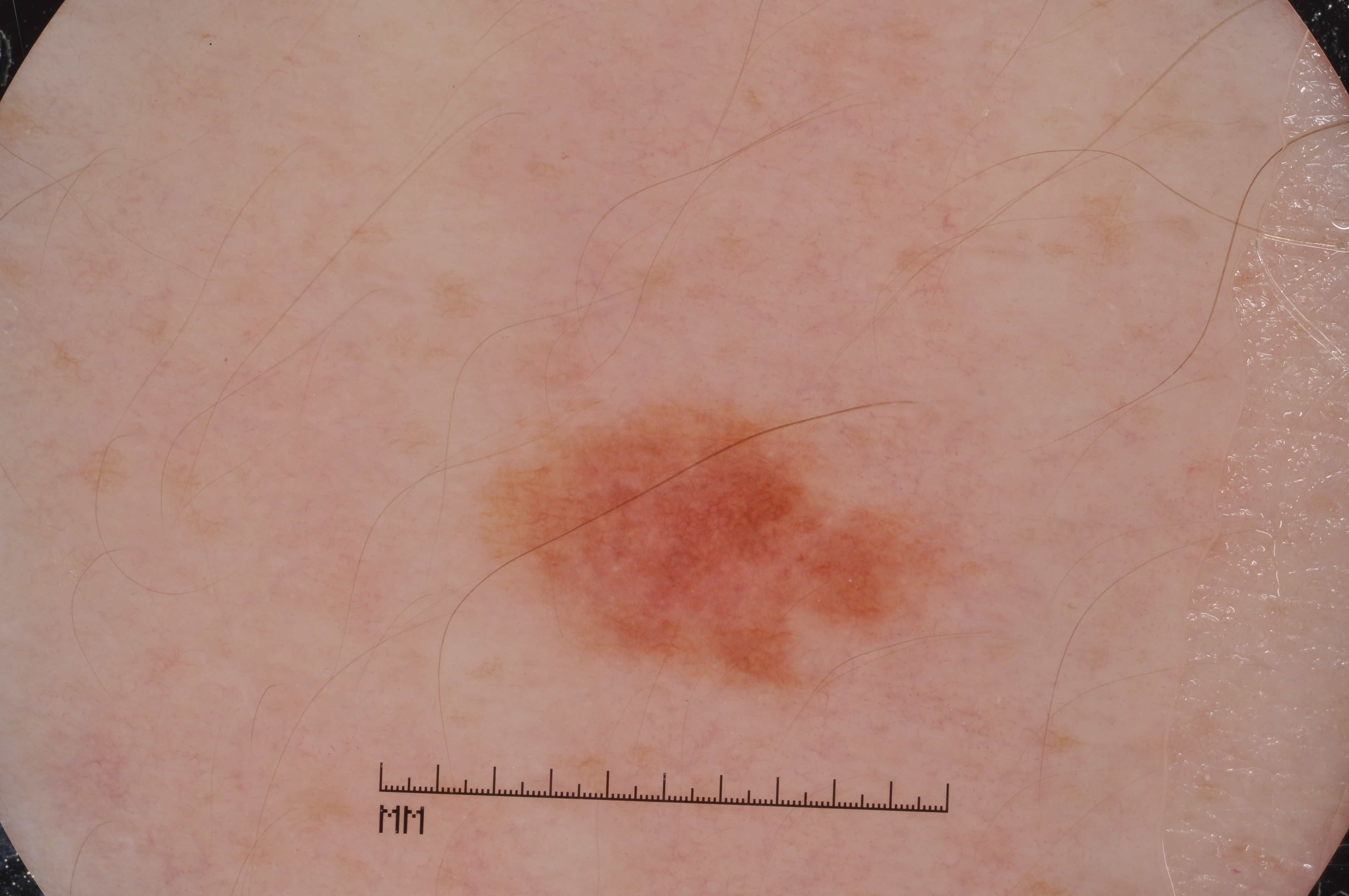This is a dermoscopic photograph of a skin lesion. Dermoscopy demonstrates pigment network and milia-like cysts. As (left, top, right, bottom), the visible lesion spans 485/399/959/686. The clinical diagnosis was a melanocytic nevus, a benign skin lesion.